Skin tone: Fitzpatrick IV · male subject, age 18–29 · a close-up photograph · reported duration is less than one week · the back of the torso and arm are involved · texture is reported as flat · symptoms reported: itching:
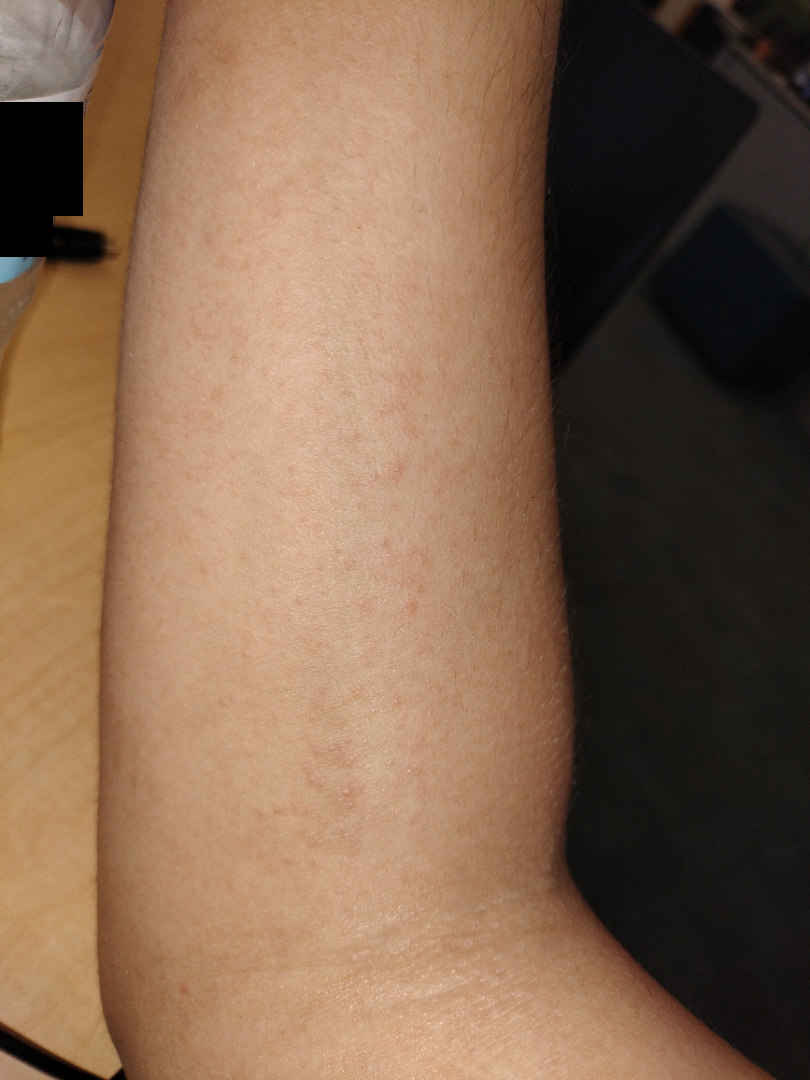Review:
On photographic review by a dermatologist: consistent with Eczema.